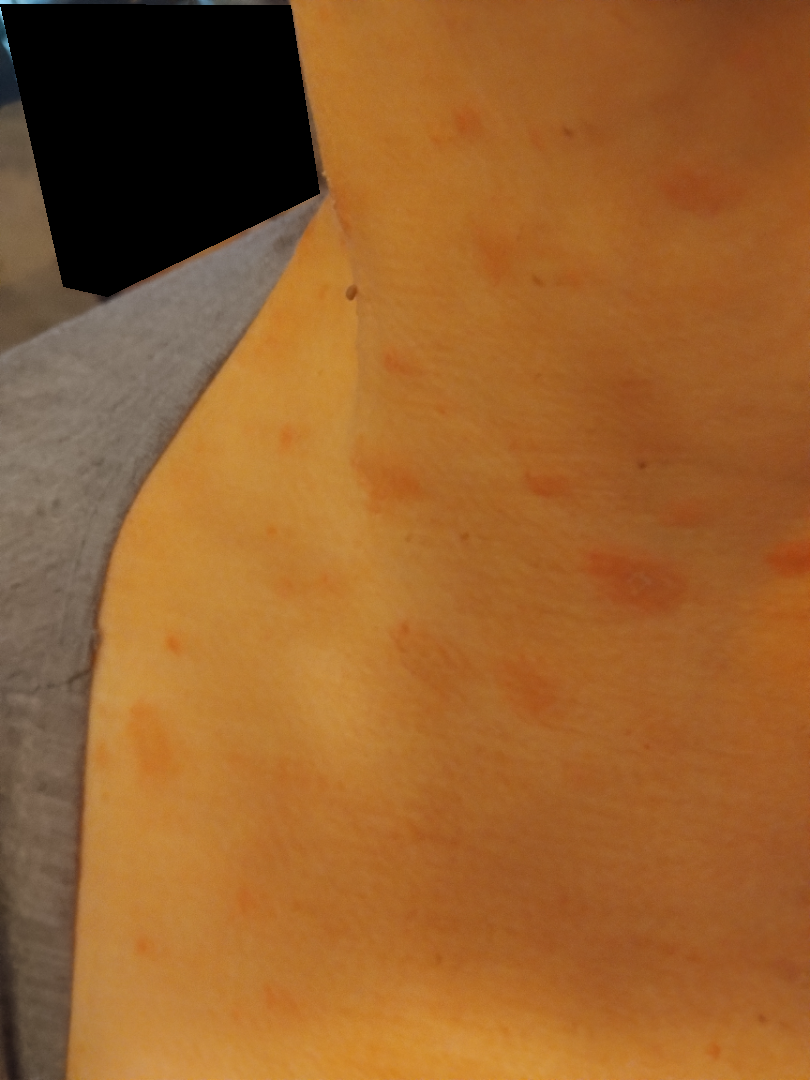Diagnostic features were not clearly distinguishable in this photograph. The head or neck, back of the torso, arm, leg and front of the torso are involved. The subject is a female aged 60–69. The photo was captured at an angle.